A dermoscopy image of a single skin lesion.
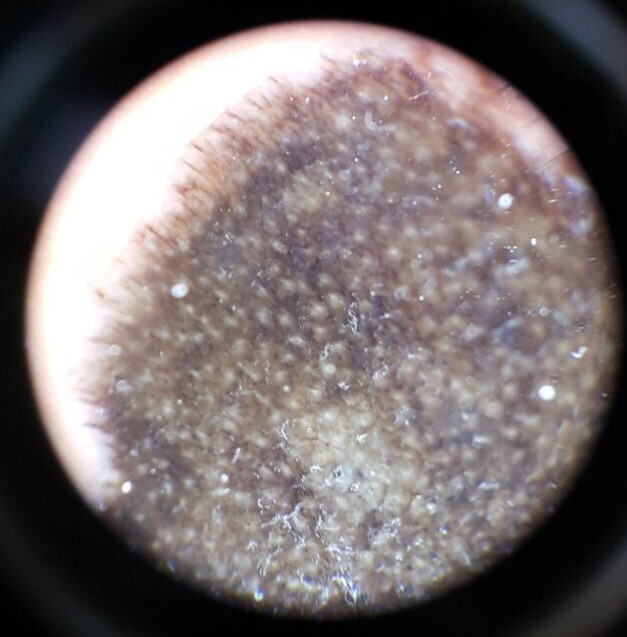Classified as a banal lesion — a congenital compound nevus.